The lesion involves the palm. This image was taken at a distance — 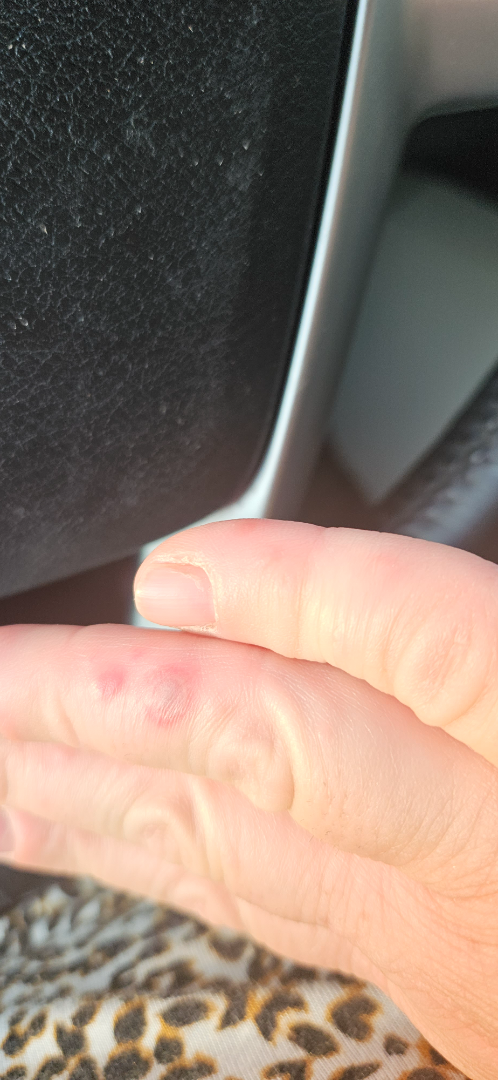duration: less than one week
symptoms:
  - bothersome appearance
  - burning
  - itching
  - pain
  - darkening
  - enlargement
patient_category: a rash
texture:
  - raised or bumpy
  - fluid-filled
systemic_symptoms: none reported
differential:
  leading:
    - Herpes Simplex
  considered:
    - Skin and soft tissue atypical mycobacterial infection
    - Eczema